Present for less than one week; the photograph is a close-up of the affected area; the patient described the issue as a rash; the lesion is associated with burning, bothersome appearance and itching; the affected area is the arm: 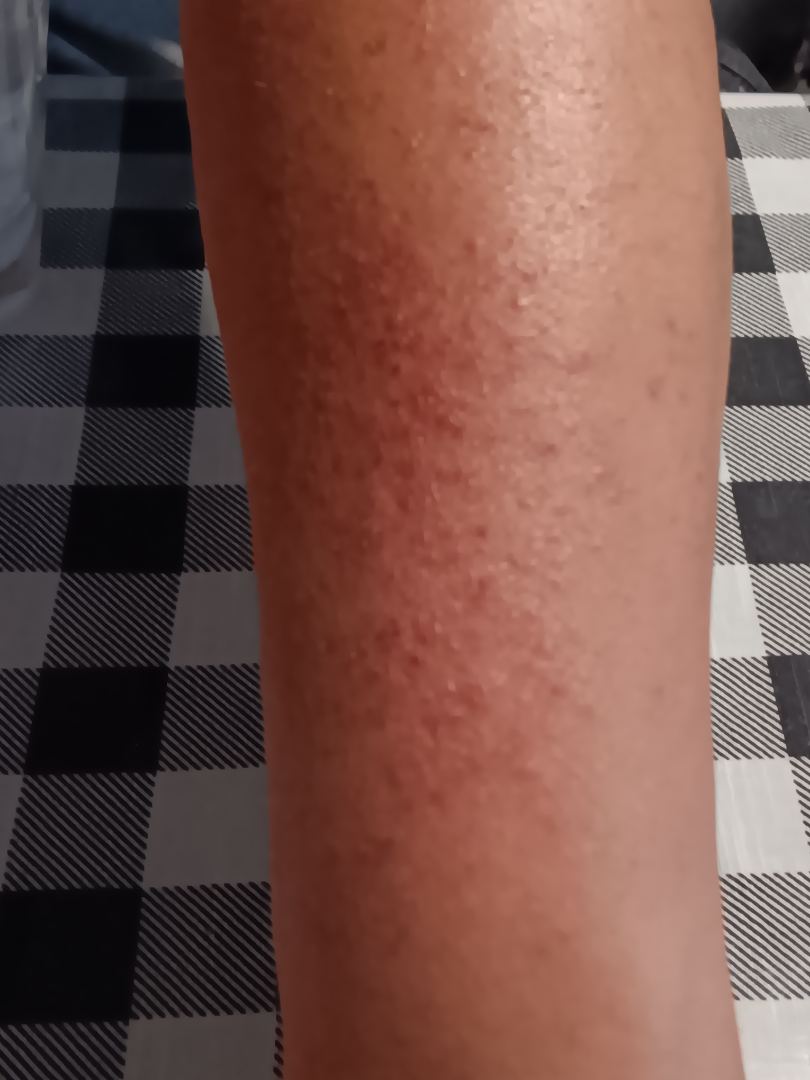  assessment: ungradable on photographic review